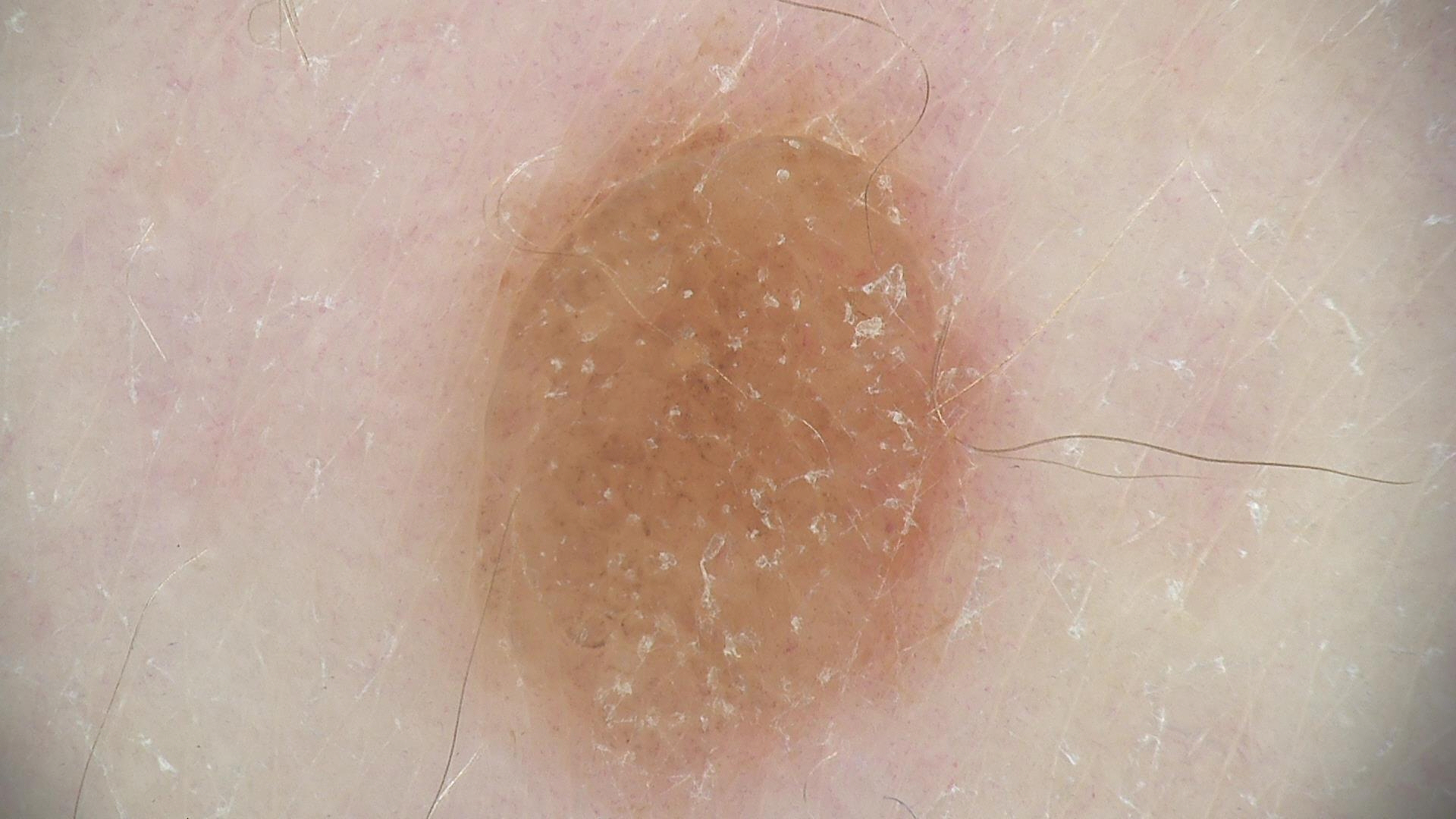– modality · dermoscopy
– classification · banal
– diagnosis · dermal nevus (expert consensus)